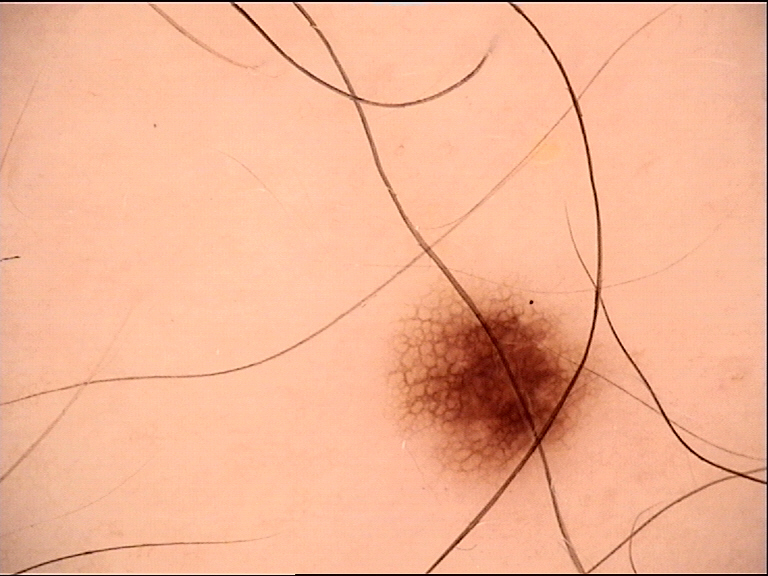Q: What is the imaging modality?
A: dermatoscopy
Q: What was the diagnostic impression?
A: dysplastic junctional nevus (expert consensus)